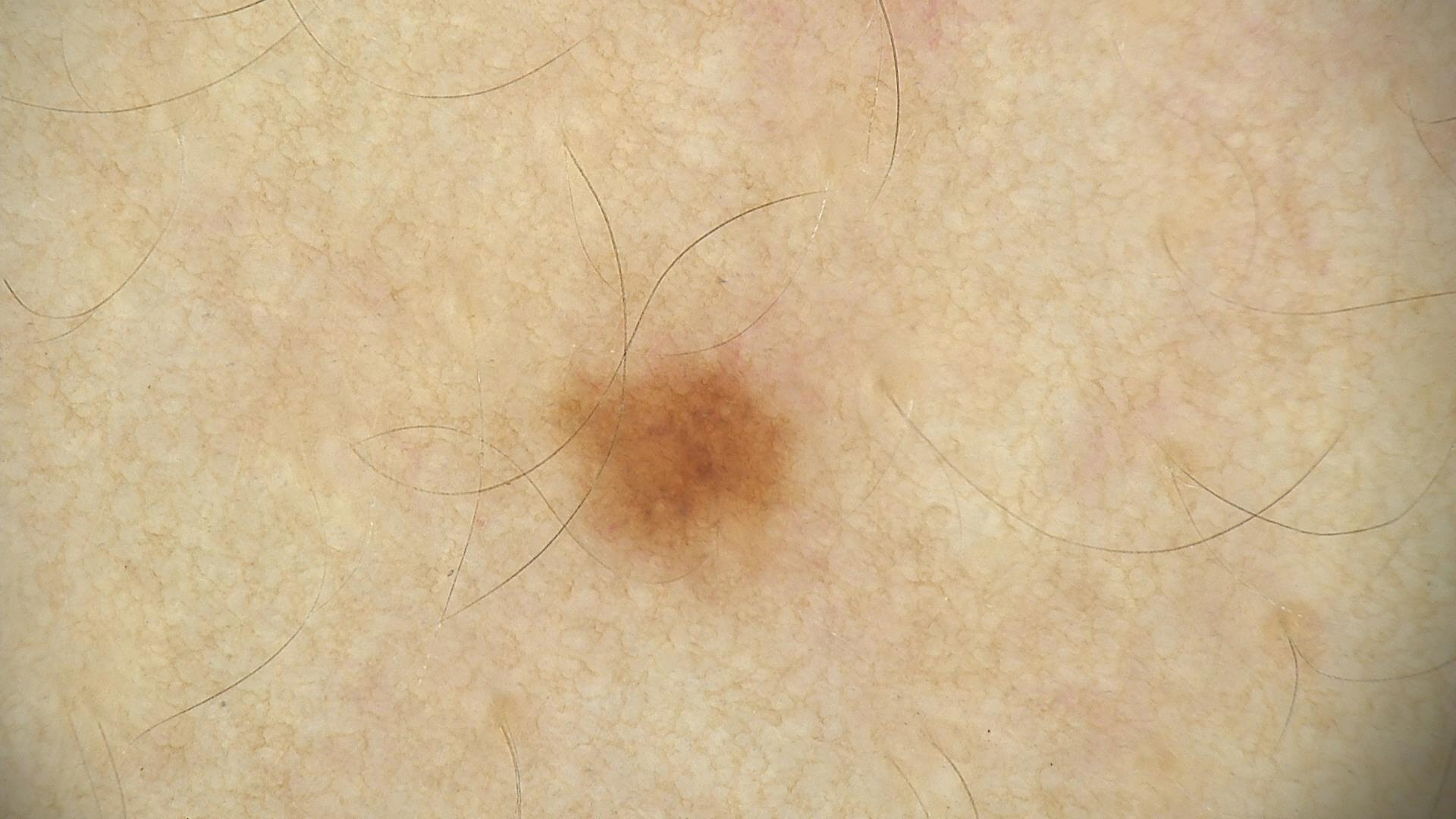<dermoscopy>
<image>dermatoscopy</image>
<diagnosis>
<name>dysplastic junctional nevus</name>
<code>jd</code>
<malignancy>benign</malignancy>
<super_class>melanocytic</super_class>
<confirmation>expert consensus</confirmation>
</diagnosis>
</dermoscopy>